A dermatoscopic image of a skin lesion.
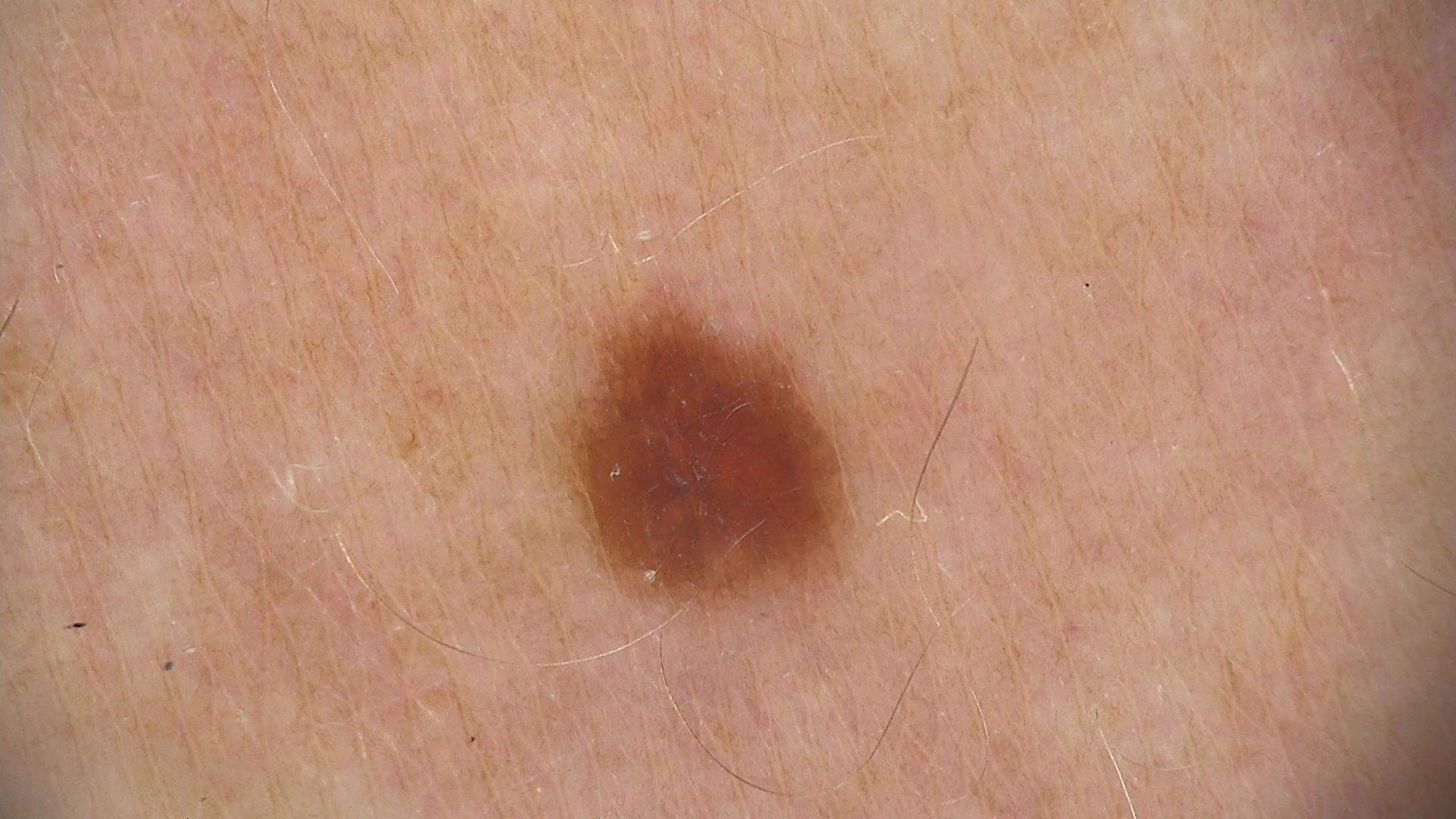Q: What is this lesion?
A: dysplastic junctional nevus (expert consensus)